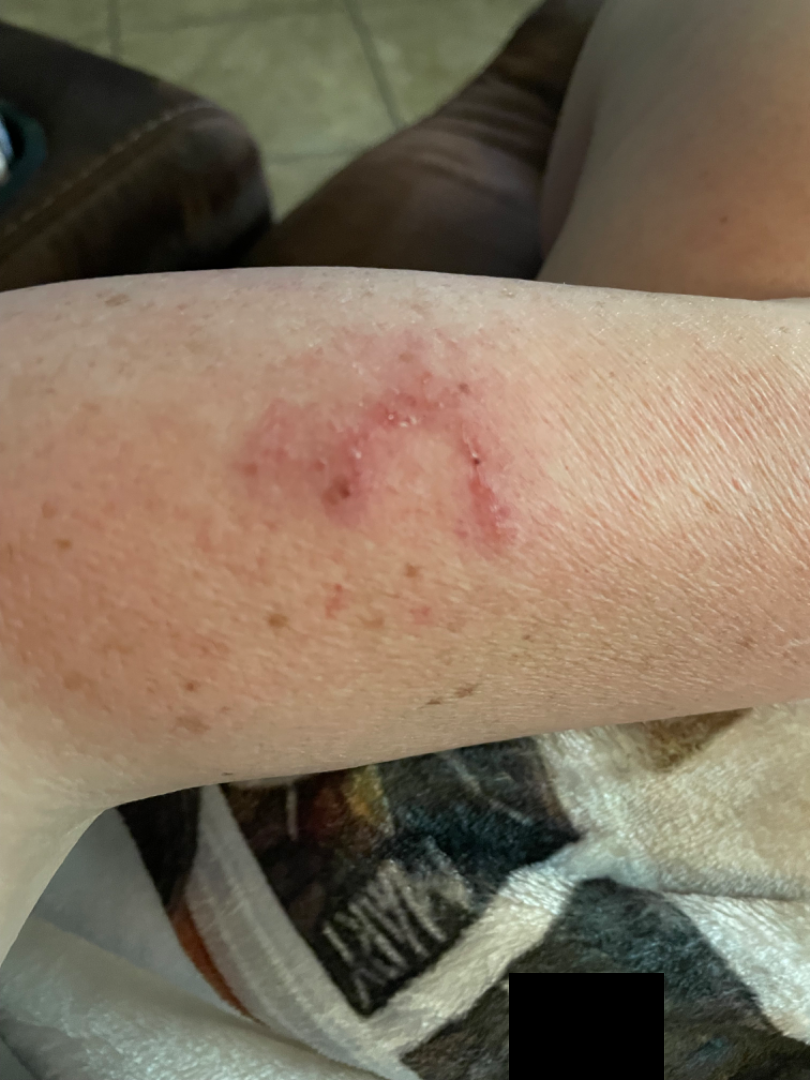Clinical context:
The contributor reports the lesion is raised or bumpy, rough or flaky and fluid-filled. The subject is a female aged 50–59. The patient described the issue as a rash. The photo was captured at an angle. The affected area is the arm. The lesion is associated with bleeding, bothersome appearance, enlargement and itching.
Assessment:
Reviewed remotely by three dermatologists: Irritant Contact Dermatitis and Tinea were considered with similar weight; a remote consideration is Eczema; less probable is Cutaneous lupus; less likely is Psoriasis.